The arm, back of the torso and front of the torso are involved; this image was taken at an angle: 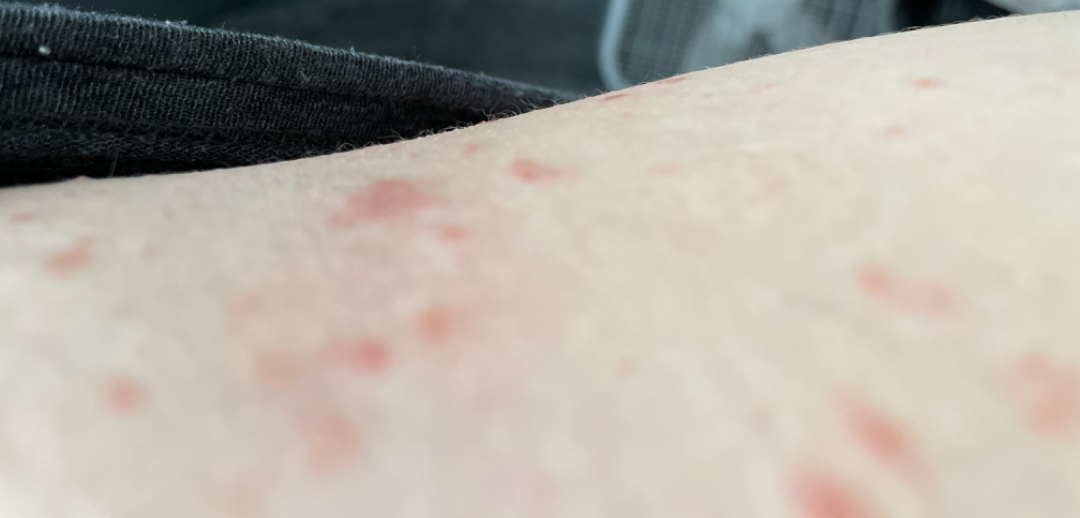The reviewing dermatologist's impression was: Hidradenitis and Abscess were considered with similar weight.